The patient says their skin reddens painfully with sun exposure · a clinical photograph showing a skin lesion · a moderate number of moles by the patient's own estimate · a female subject 81 years of age — 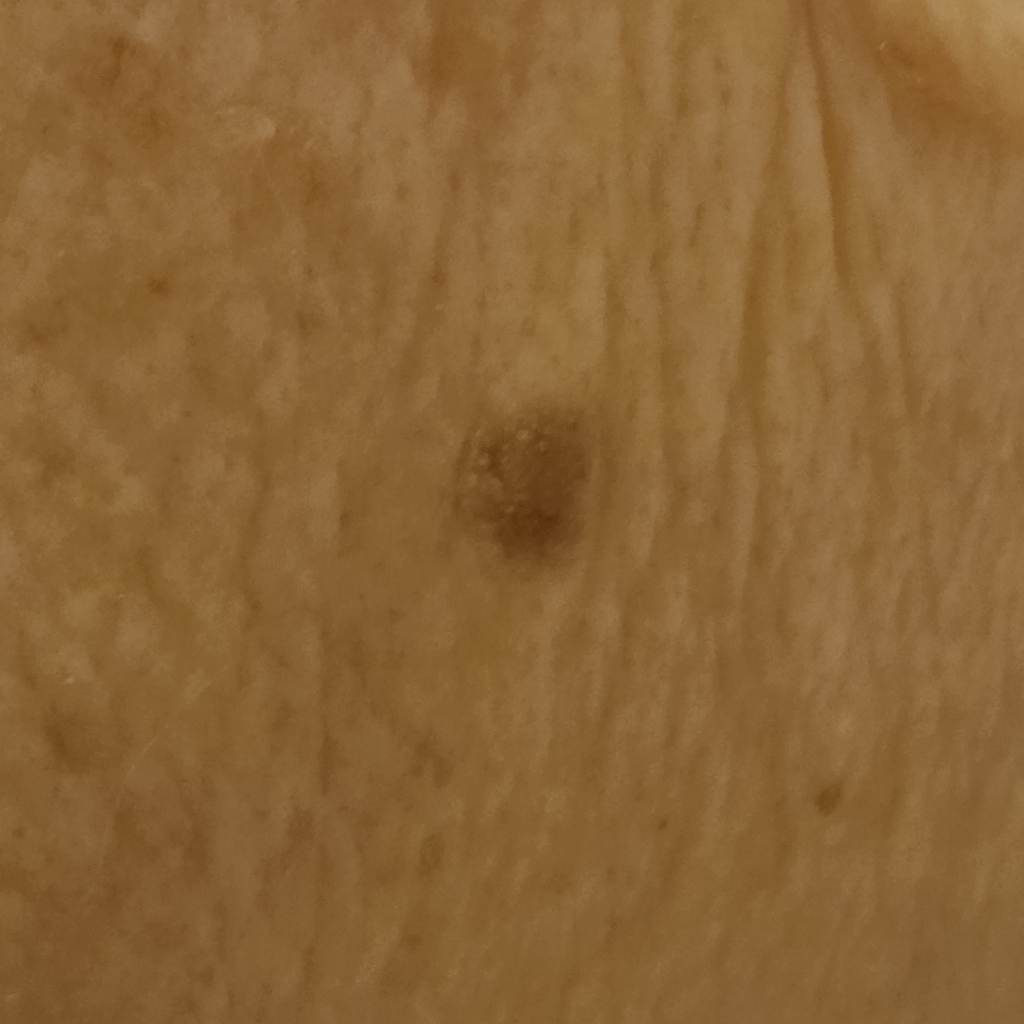Q: What is the anatomic site?
A: the face
Q: How large is the lesion?
A: 5.3 mm
Q: What was the diagnosis?
A: seborrheic keratosis (dermatologist consensus)